The patient says their skin reddens painfully with sun exposure · the patient describes having numerous moles · a male patient 65 years old · imaged for a research study, with no referral diagnosis recorded · a clinical photograph of a skin lesion: 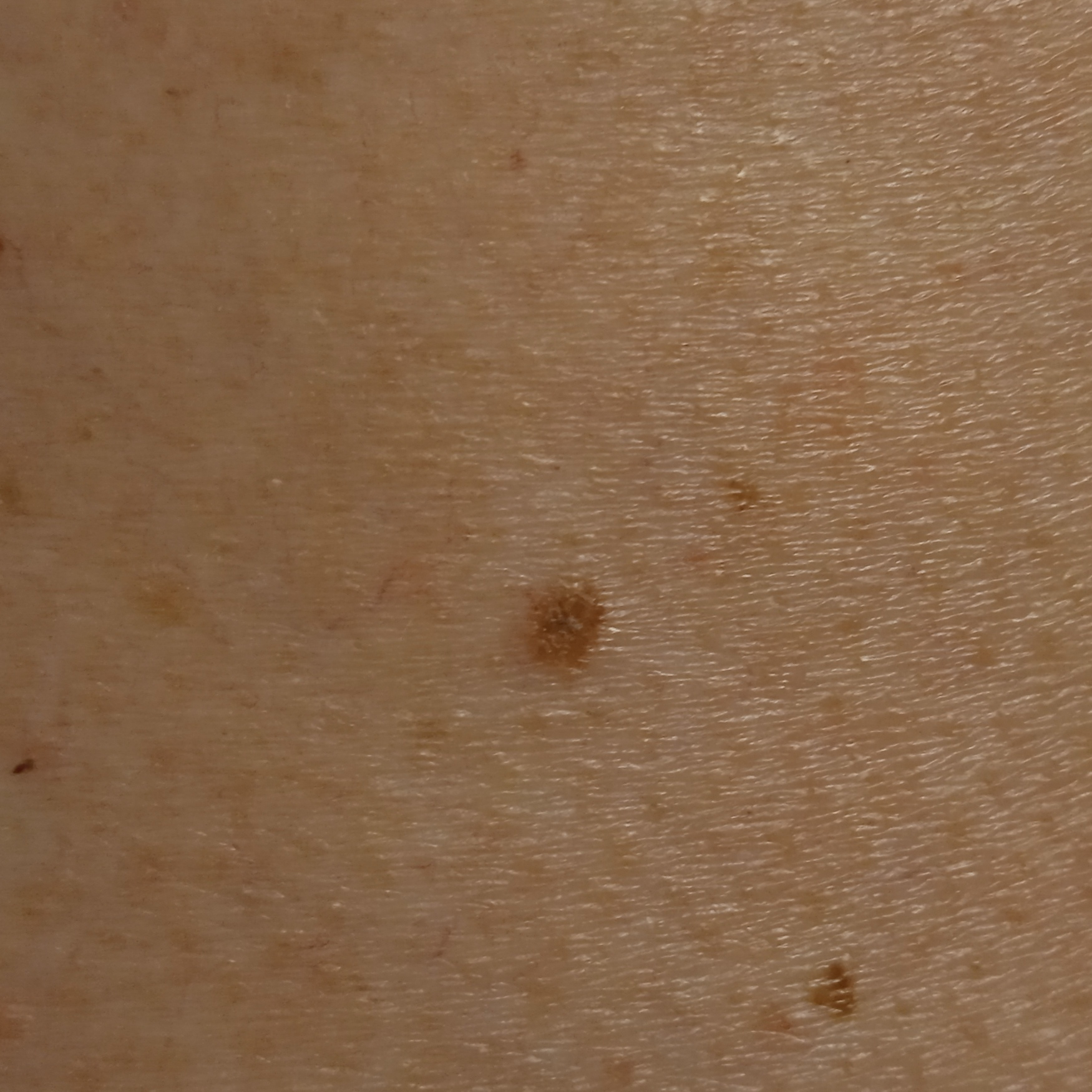location — the back
assessment — seborrheic keratosis (dermatologist consensus)